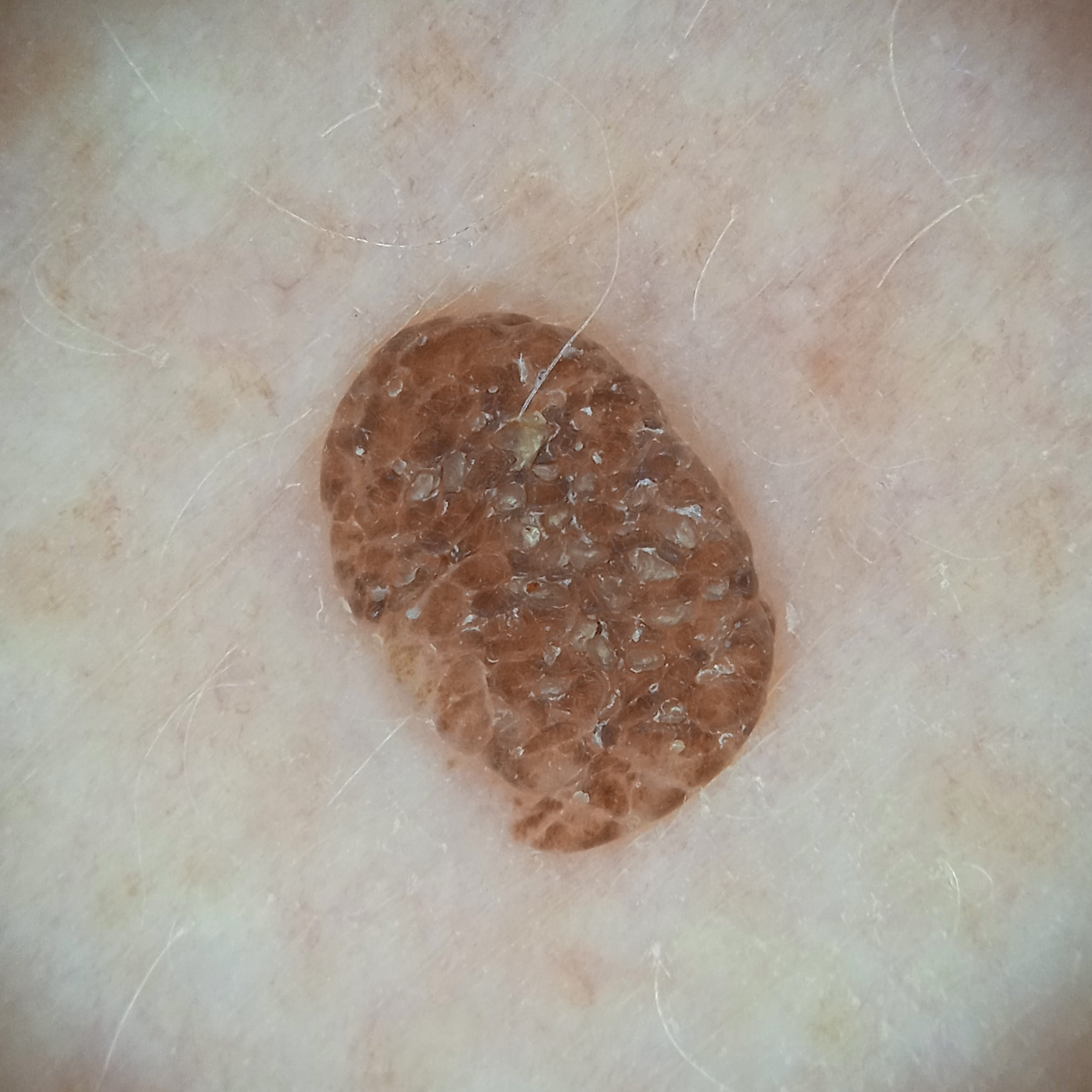Assessment: Dermatologist review favored a seborrheic keratosis.